Self-categorized by the patient as a rash. The photograph was taken at an angle. Fitzpatrick III; lay reviewers estimated MST 3 or 4. The affected area is the front of the torso, arm, back of the hand and back of the torso. The contributor is a male aged 60–69. Texture is reported as raised or bumpy. Present for about one day. The lesion is associated with burning and itching: 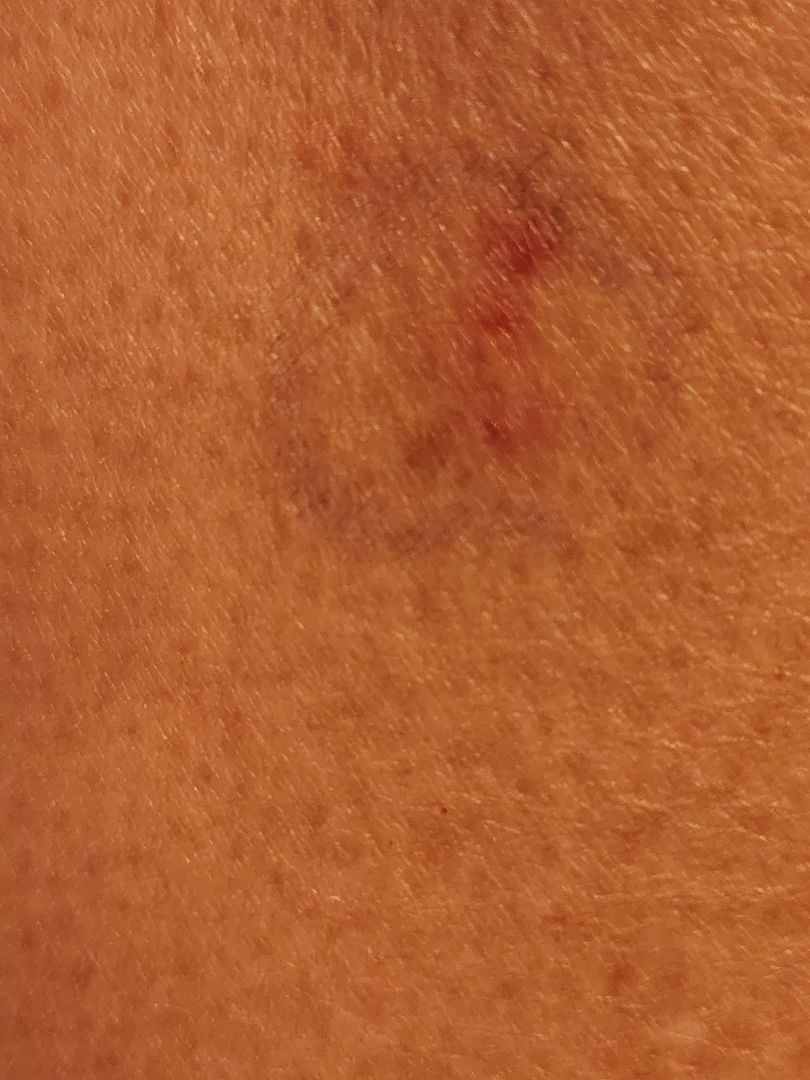Q: What is the differential diagnosis?
A: most consistent with Dermatofibroma; also consider Insect Bite